A dermoscopic image of a skin lesion:
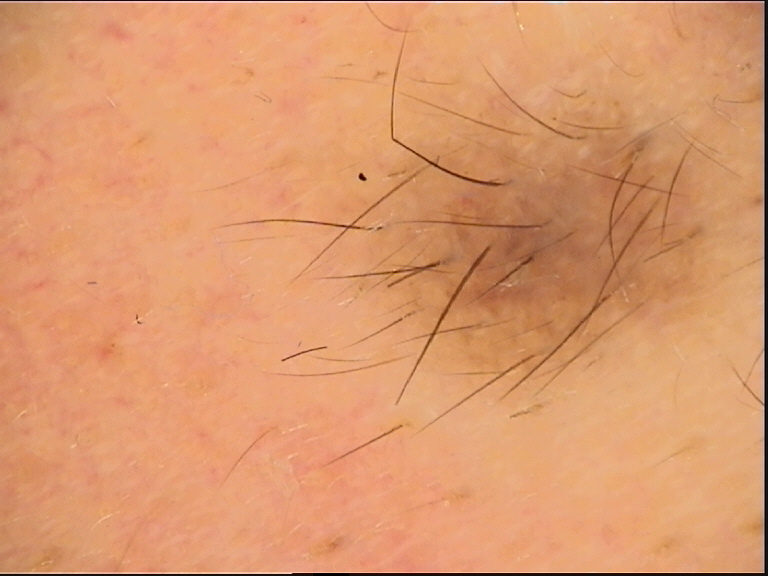Impression: Consistent with a Miescher nevus.